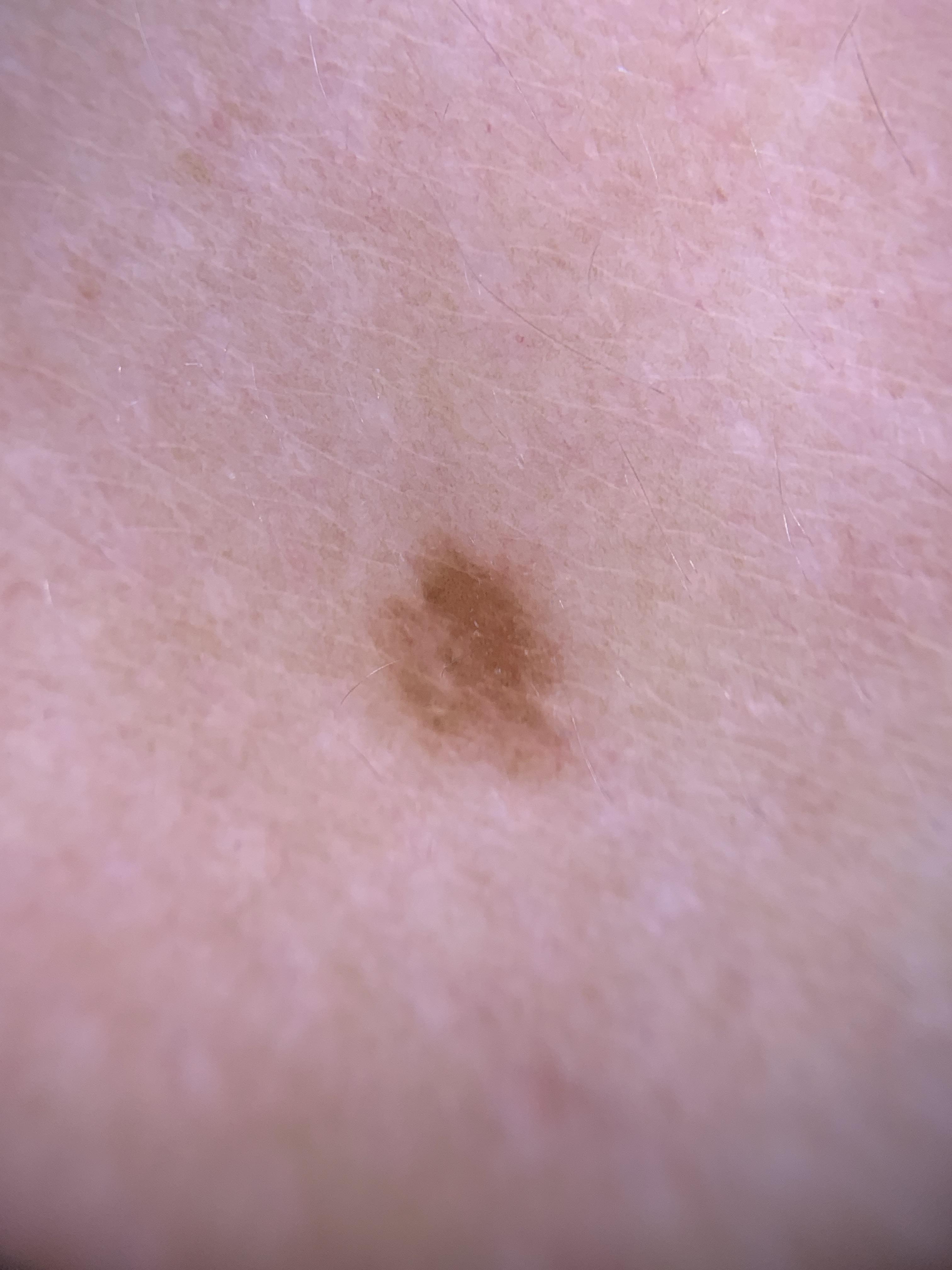image type — dermoscopic image | patient — female, aged around 25 | impression — Nevus.